The lesion involves the leg; the photograph was taken at an angle: 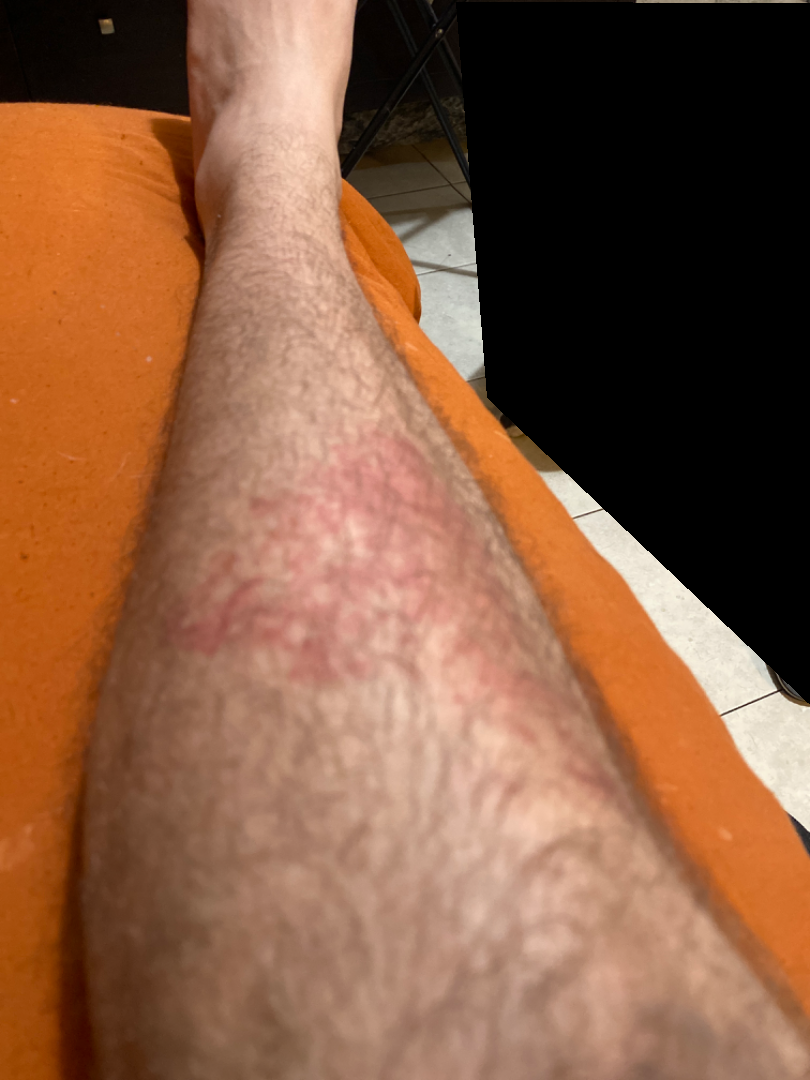The image was not sufficient for the reviewer to characterize the skin condition.